A dermoscopic photograph of a skin lesion: 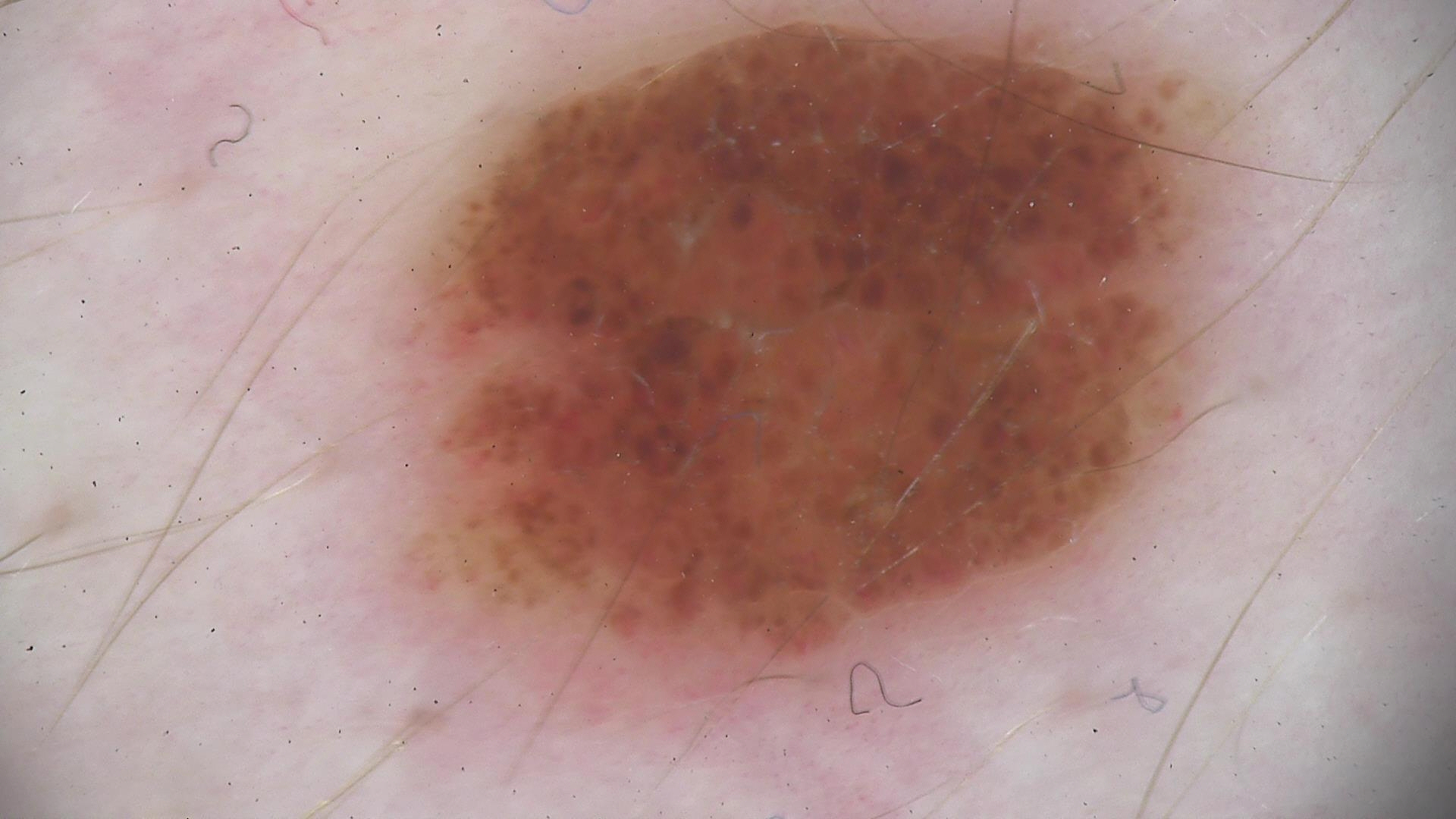subtype = banal
label = compound nevus (expert consensus)